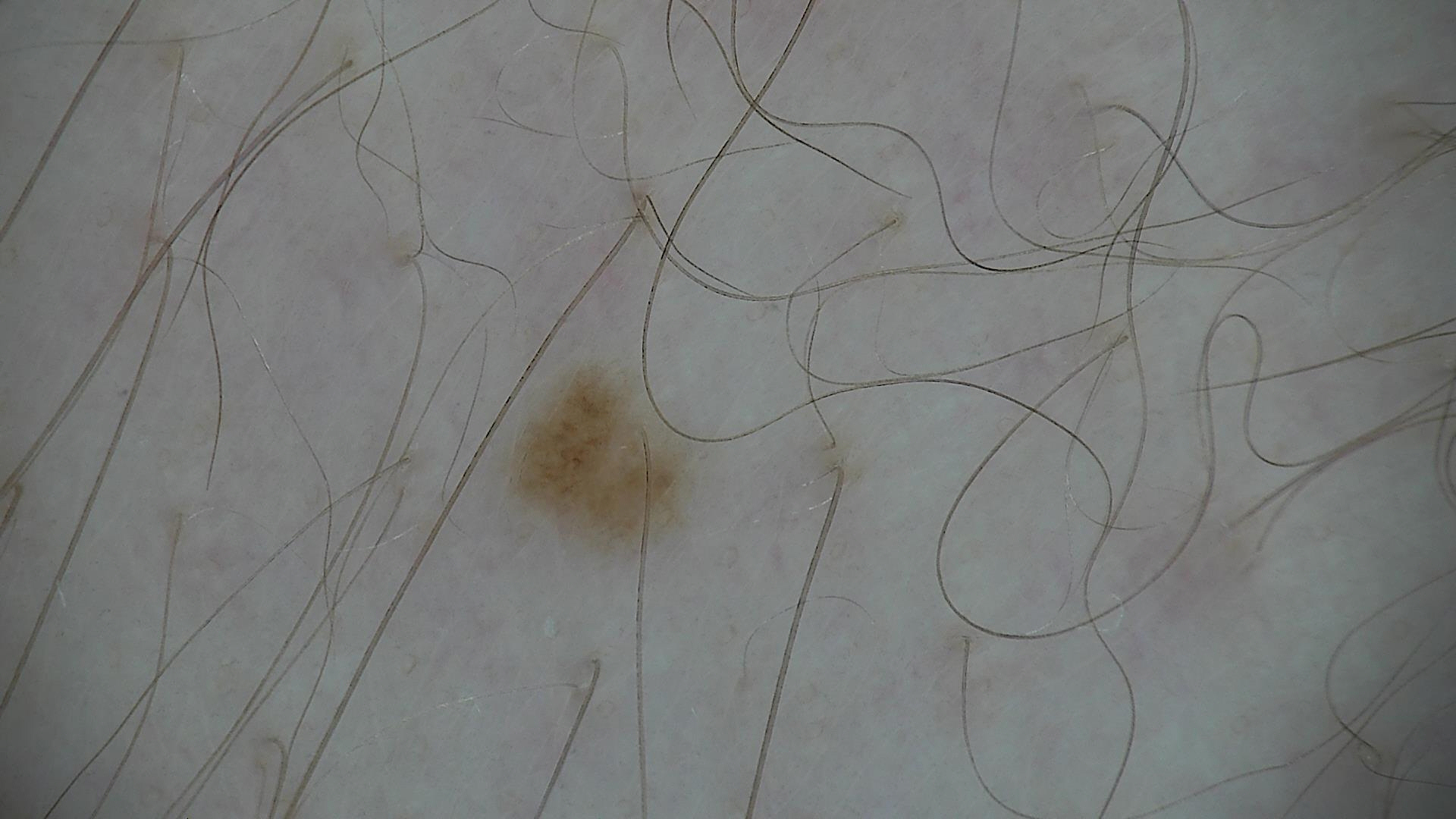Dermoscopy of a skin lesion. The diagnostic label was a dysplastic junctional nevus.